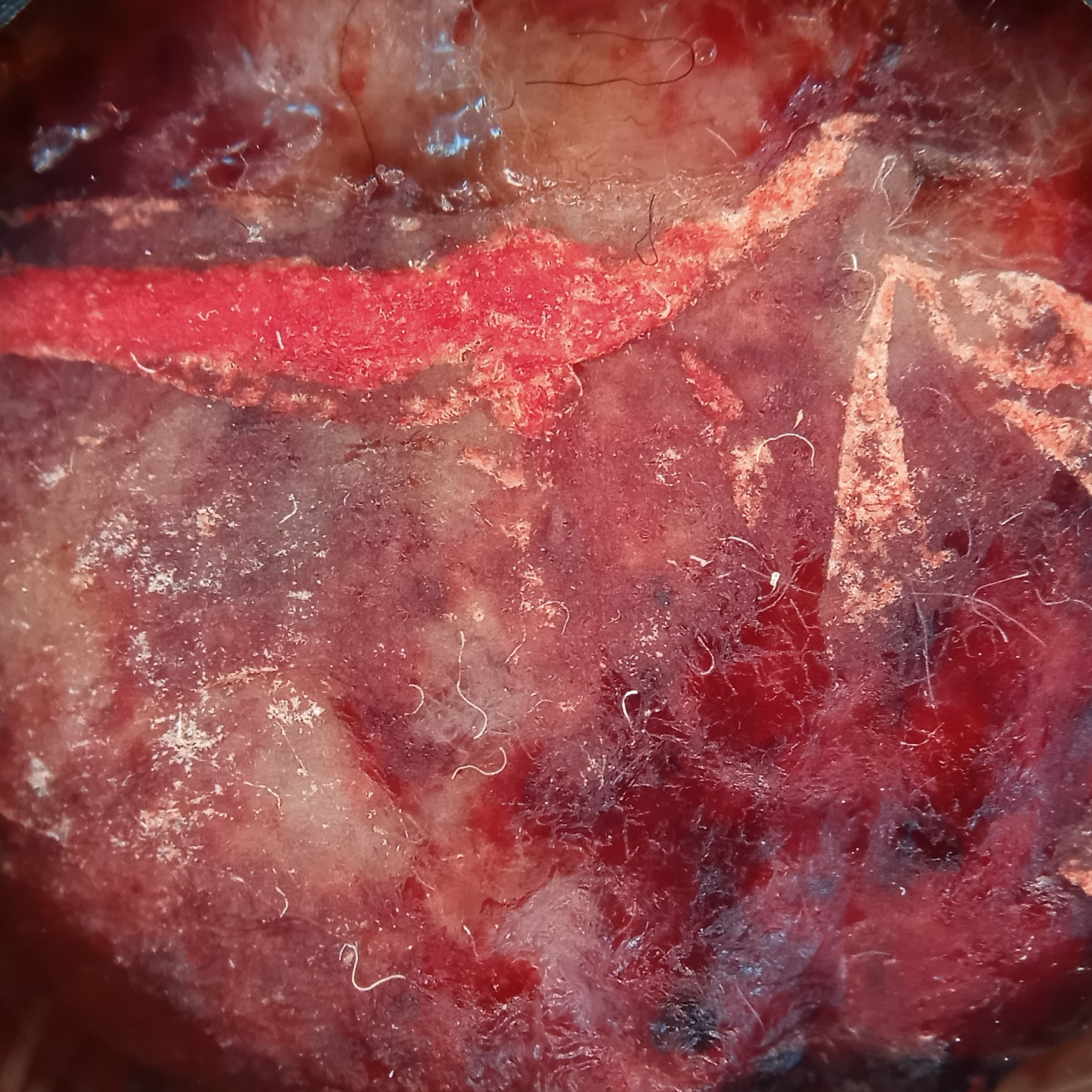patient: male, age 78; site: the face; diameter: 19.9 mm; pathology: melanoma (biopsy-proven).